A skin lesion imaged with a dermatoscope:
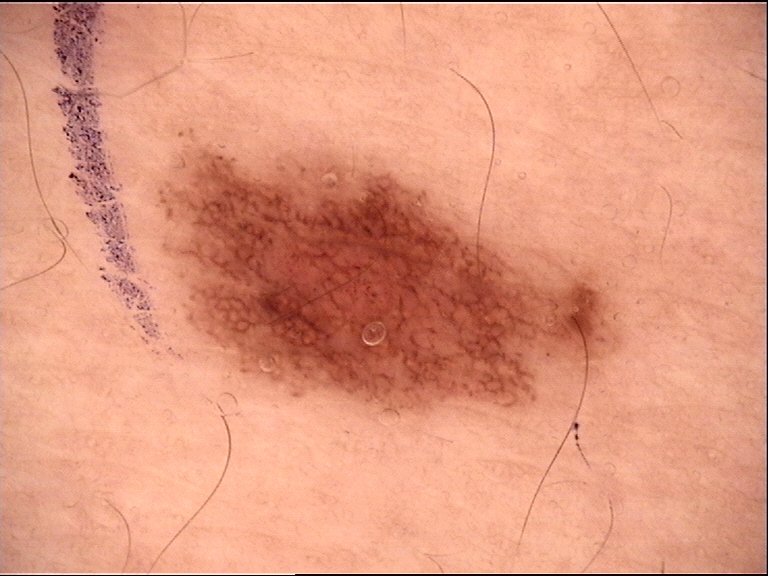The diagnostic label was a banal lesion — a junctional nevus.